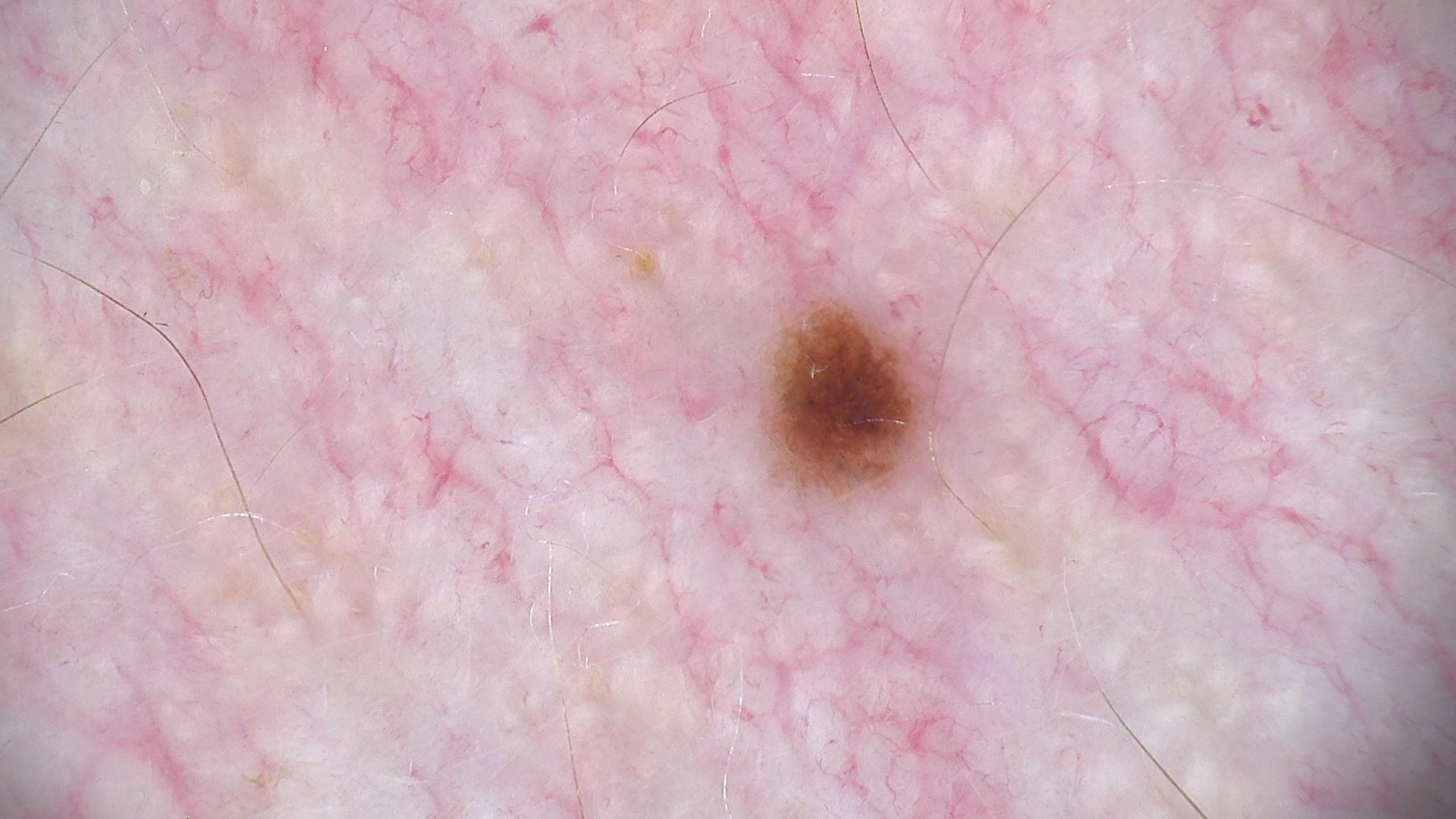Conclusion:
The diagnosis was a dysplastic junctional nevus.